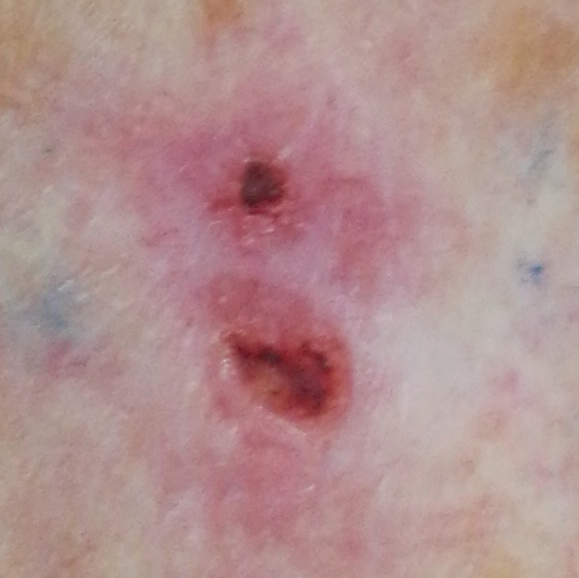patient: female, age 79 | image type: clinical photograph | symptoms: itching, elevation | diagnosis: basal cell carcinoma (biopsy-proven).